Dermoscopy of a skin lesion.
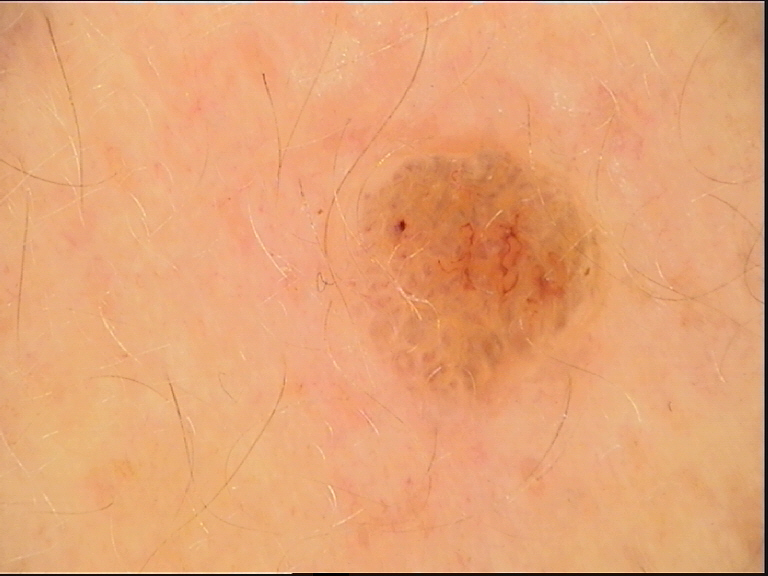label = seborrheic keratosis (expert consensus).